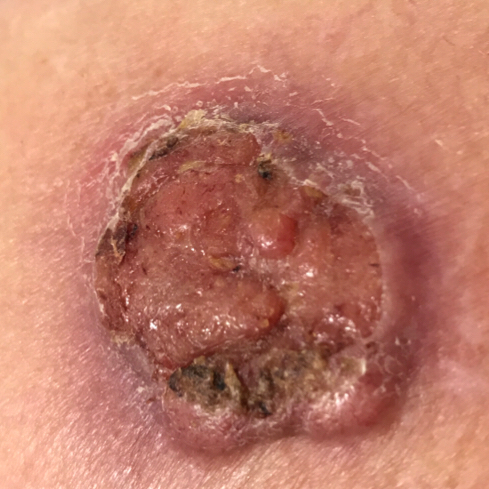Findings: A female subject in their early 80s. FST II. The lesion involves the back. The lesion measures 35 × 33 mm. By the patient's account, the lesion hurts, is elevated, has bled, and itches. Conclusion: On biopsy, the diagnosis was a malignant lesion — a squamous cell carcinoma.